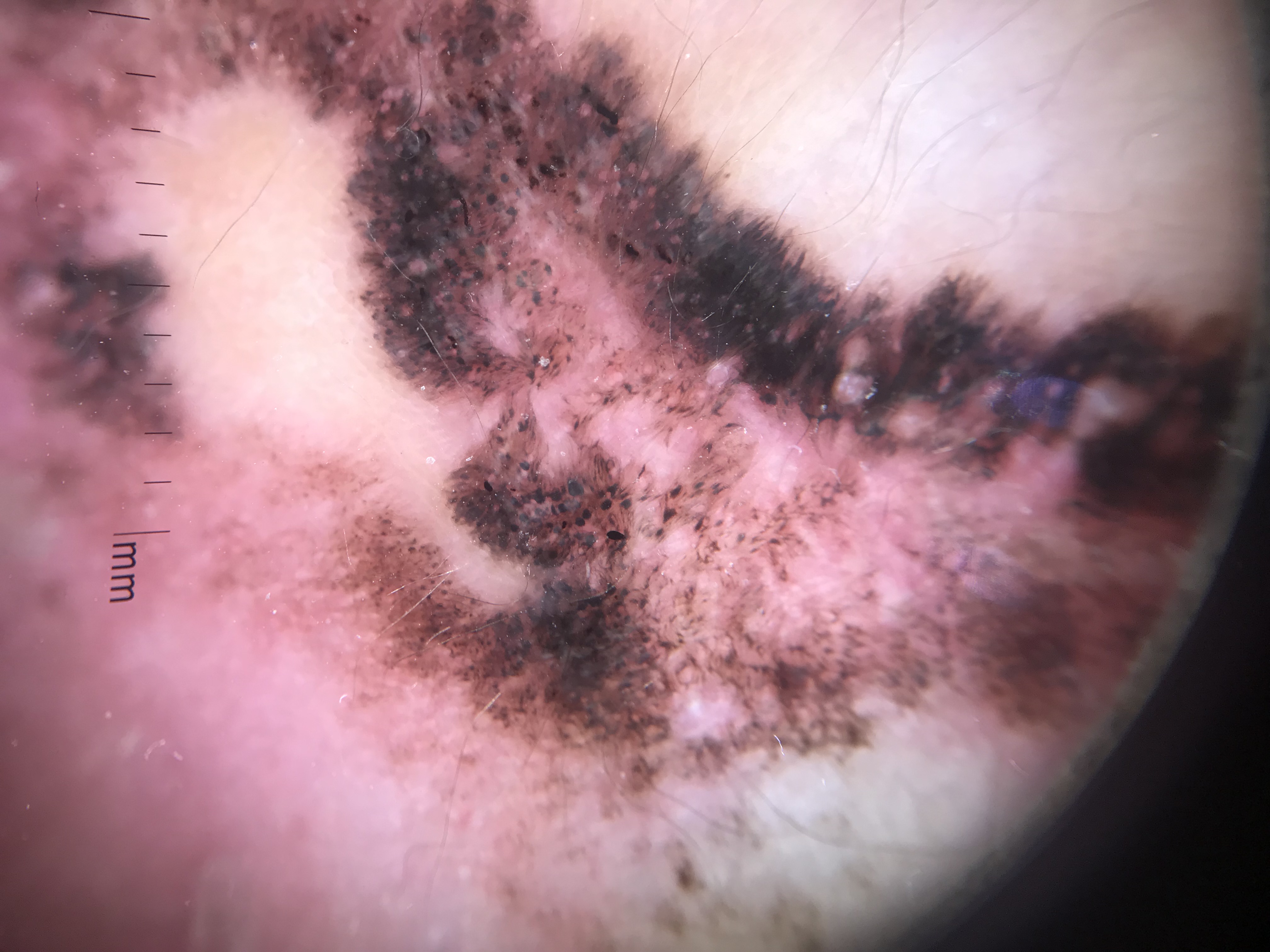Q: What did the workup show?
A: melanoma (biopsy-proven)